A dermoscopic image of a skin lesion.
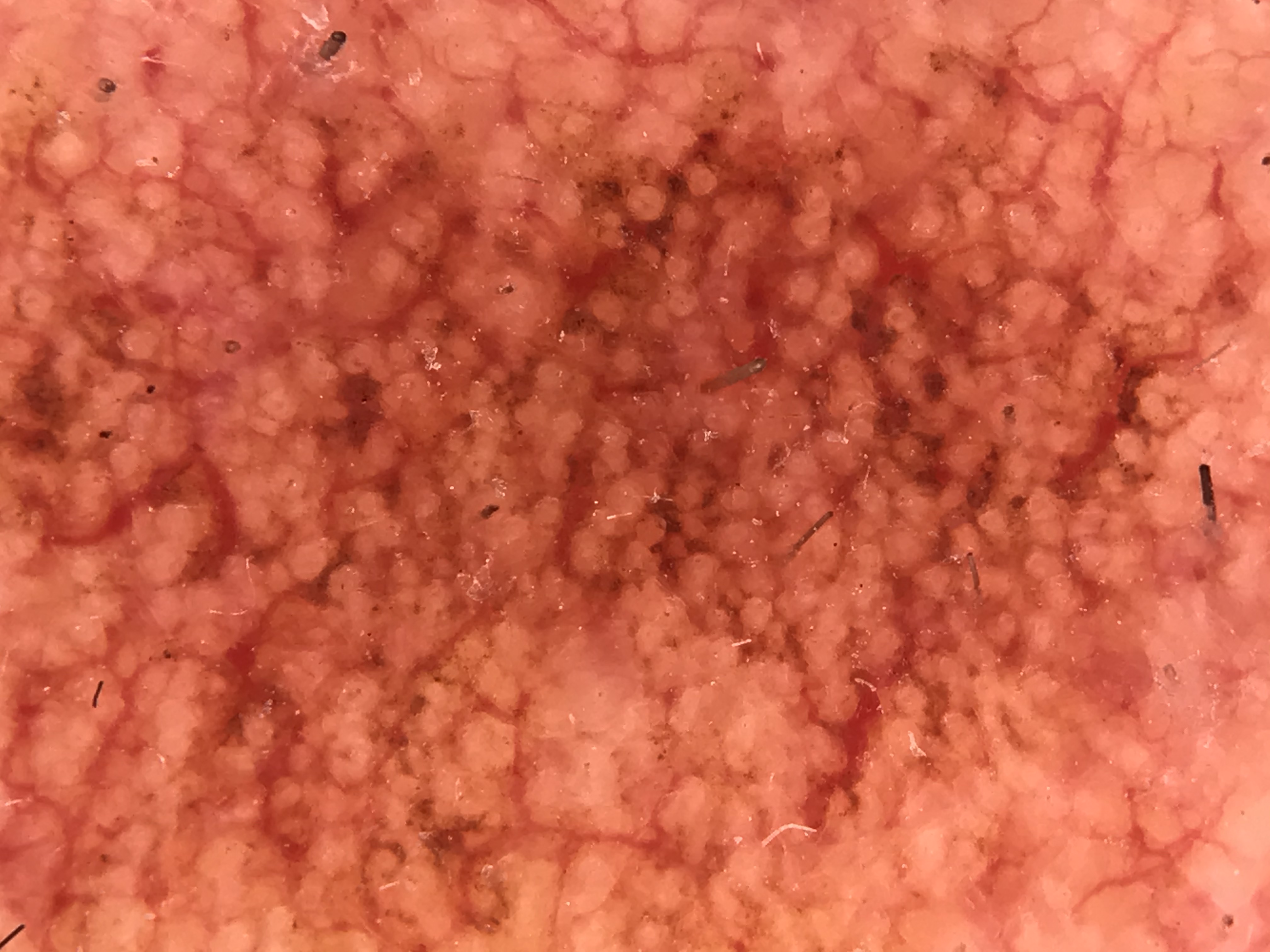The morphology is that of a keratinocytic lesion. Classified as a lesion of indeterminate malignant potential — an actinic keratosis.